A clinical photograph showing a skin lesion; a subject aged 54:
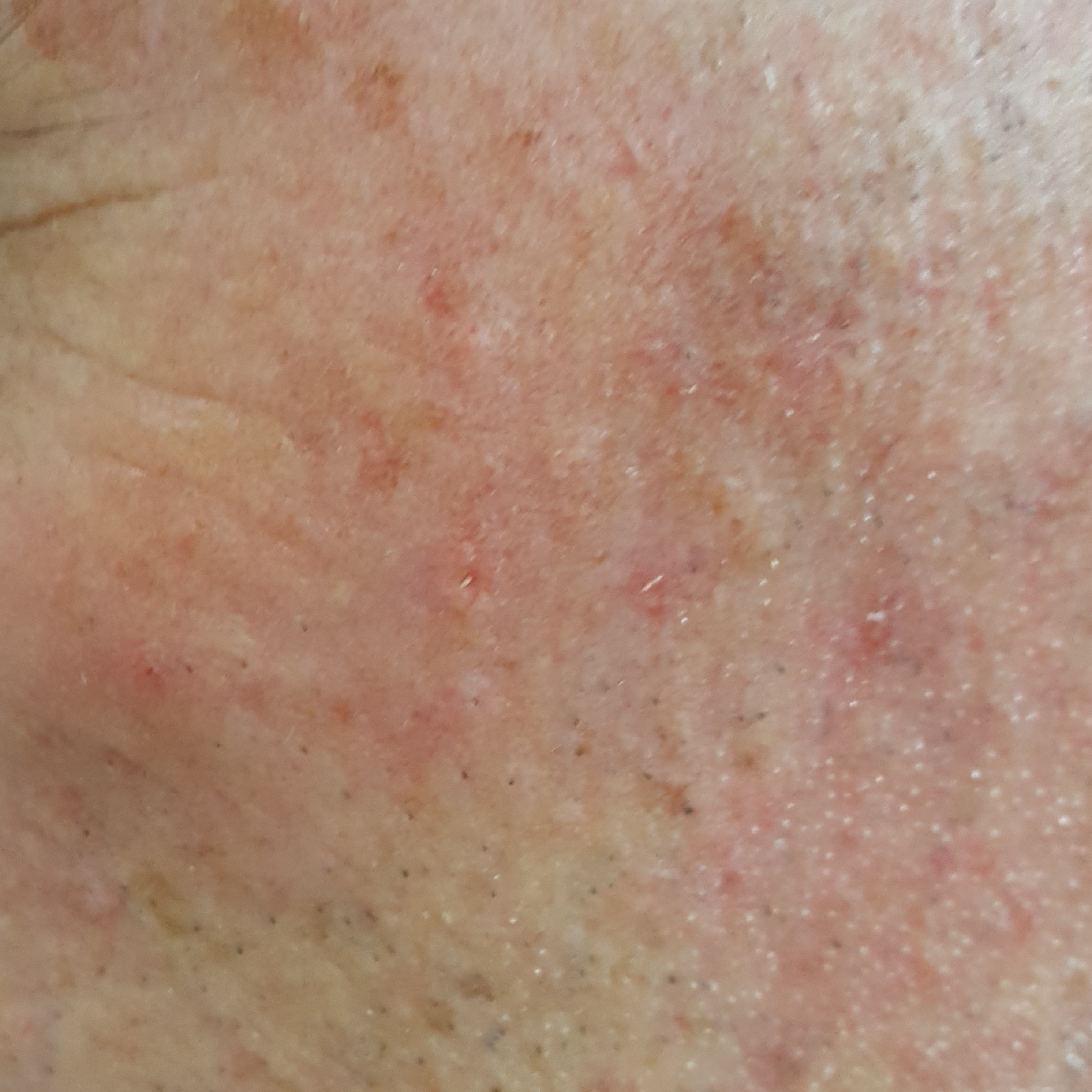<skin_lesion>
<lesion_location>the face</lesion_location>
<diagnosis>
<name>actinic keratosis</name>
<code>ACK</code>
<malignancy>indeterminate</malignancy>
<confirmation>clinical consensus</confirmation>
</diagnosis>
</skin_lesion>